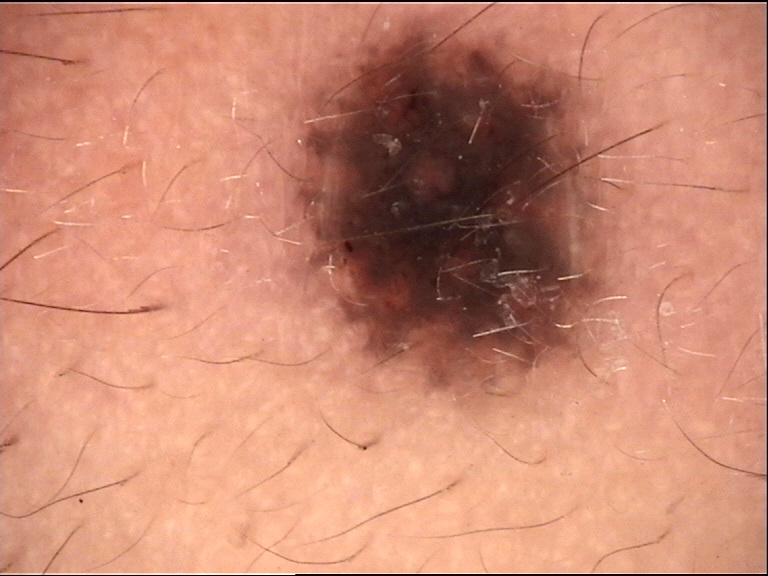category = banal, class = compound nevus (expert consensus).